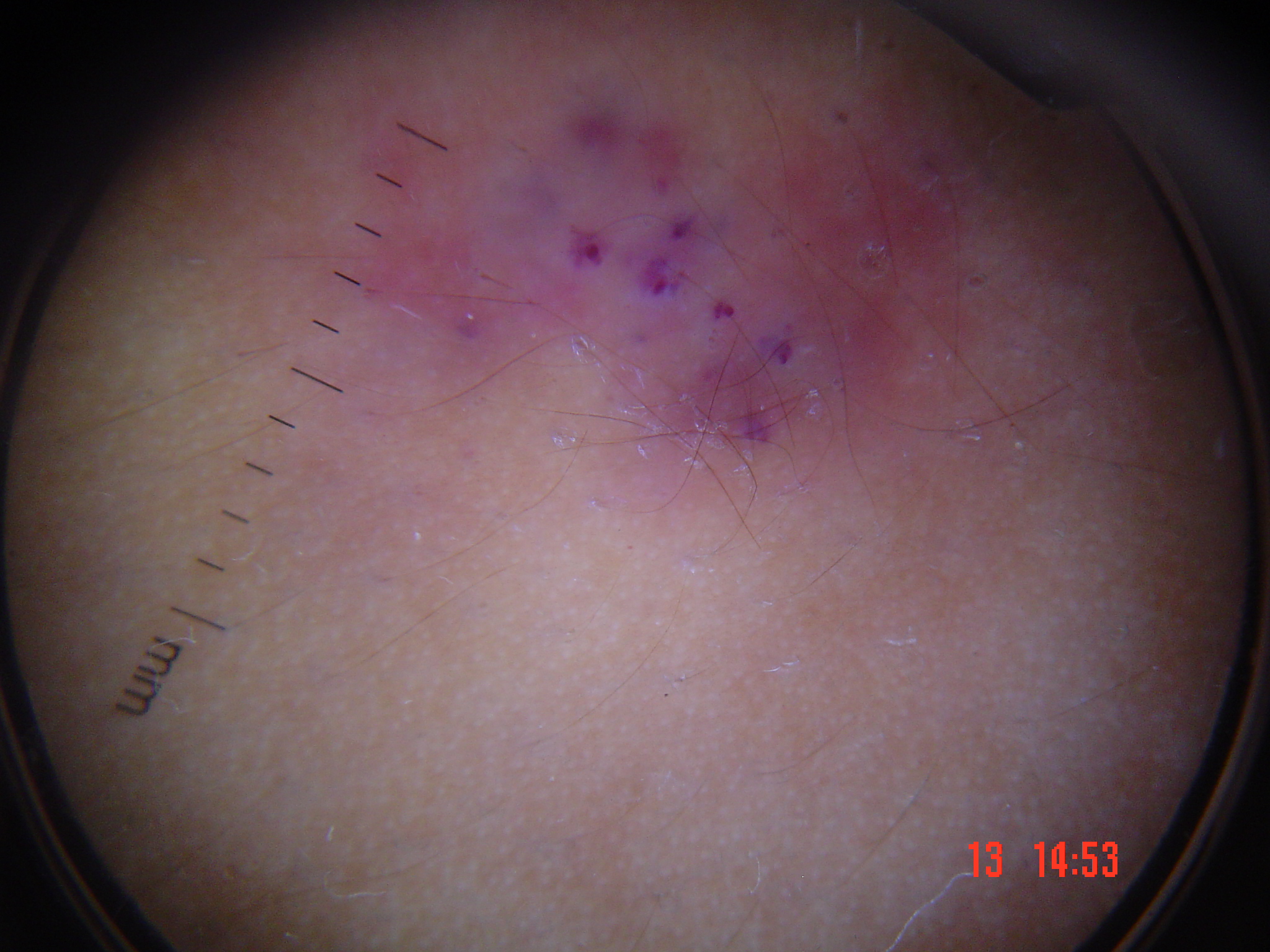Q: What was the diagnostic impression?
A: angiokeratoma (expert consensus)